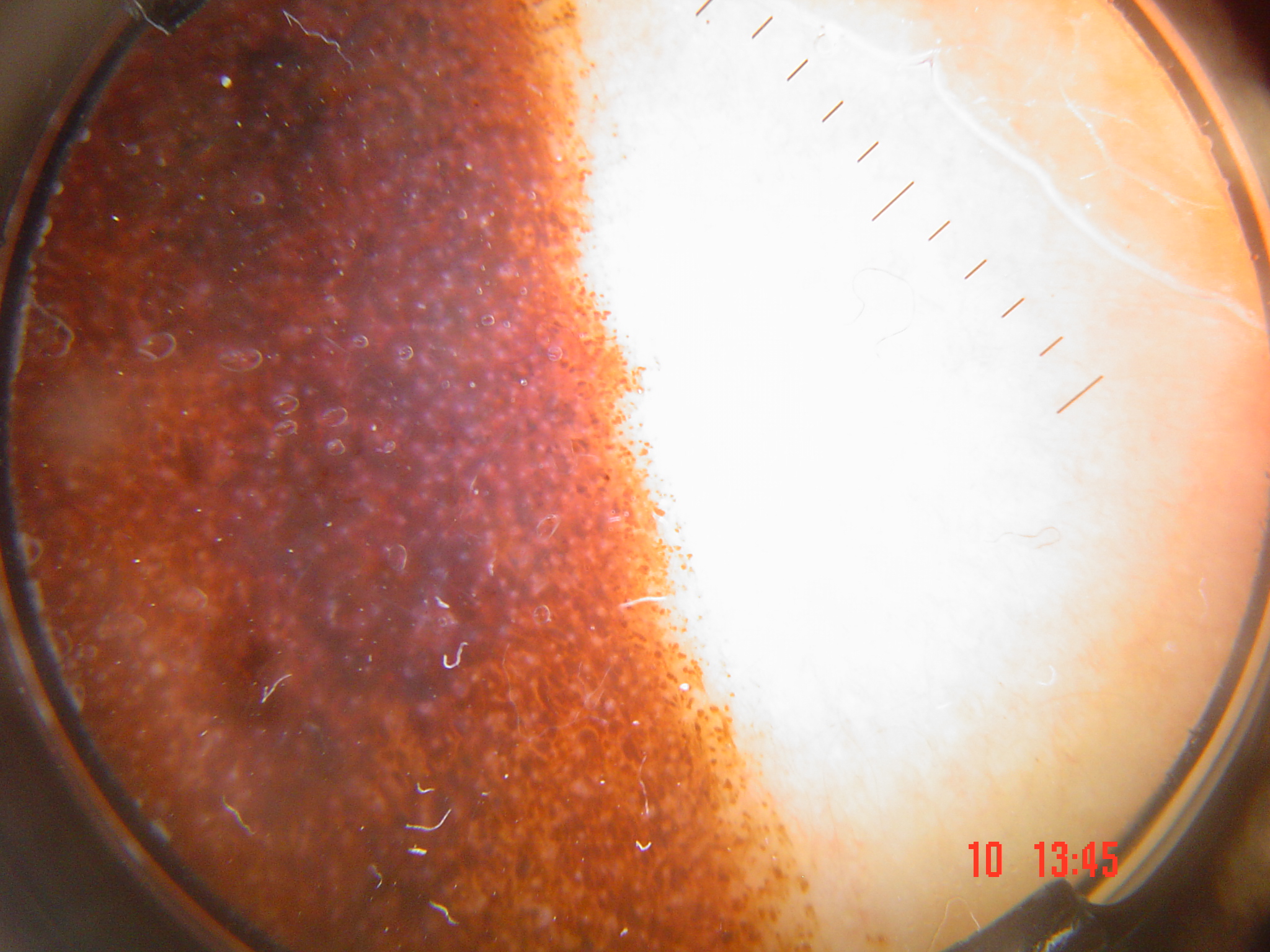image type: dermoscopy | diagnostic label: congenital compound nevus (expert consensus).